Recorded as Fitzpatrick phototype II; the chart records prior malignancy (patient or family), pesticide exposure, and no prior skin cancer (patient or family); a smartphone photograph of a skin lesion:
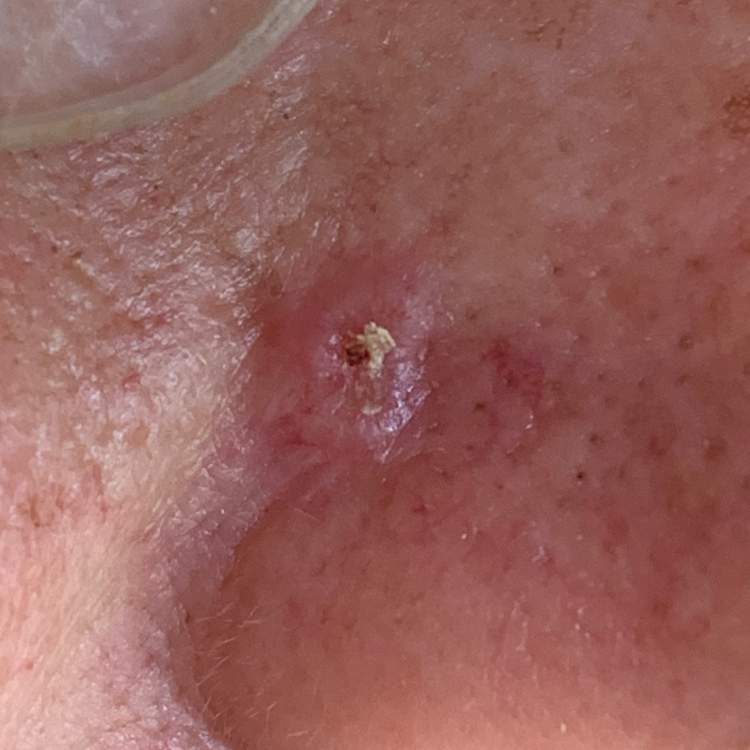body site = the nose
lesion diameter = 5 × 5 mm
patient-reported symptoms = bleeding, elevation, growth, pain
diagnostic label = basal cell carcinoma (biopsy-proven)